A dermatoscopic image of a skin lesion.
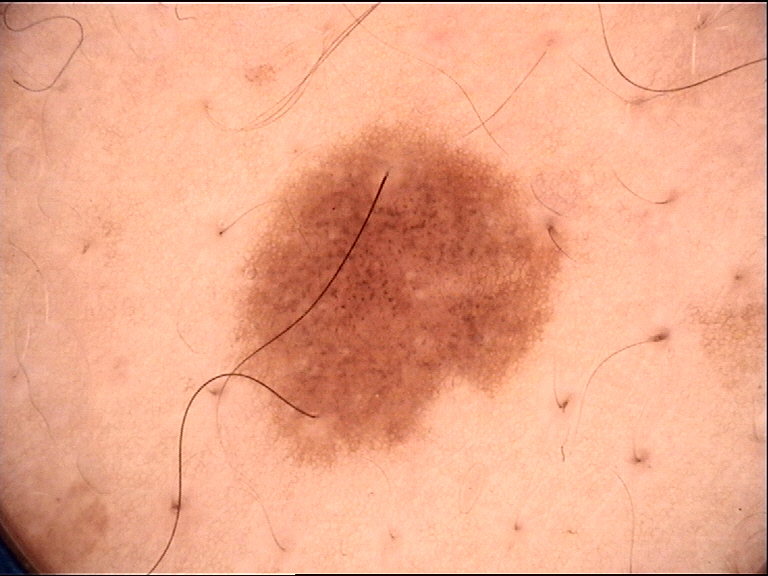{
  "diagnosis": {
    "name": "dysplastic junctional nevus",
    "code": "jd",
    "malignancy": "benign",
    "super_class": "melanocytic",
    "confirmation": "expert consensus"
  }
}